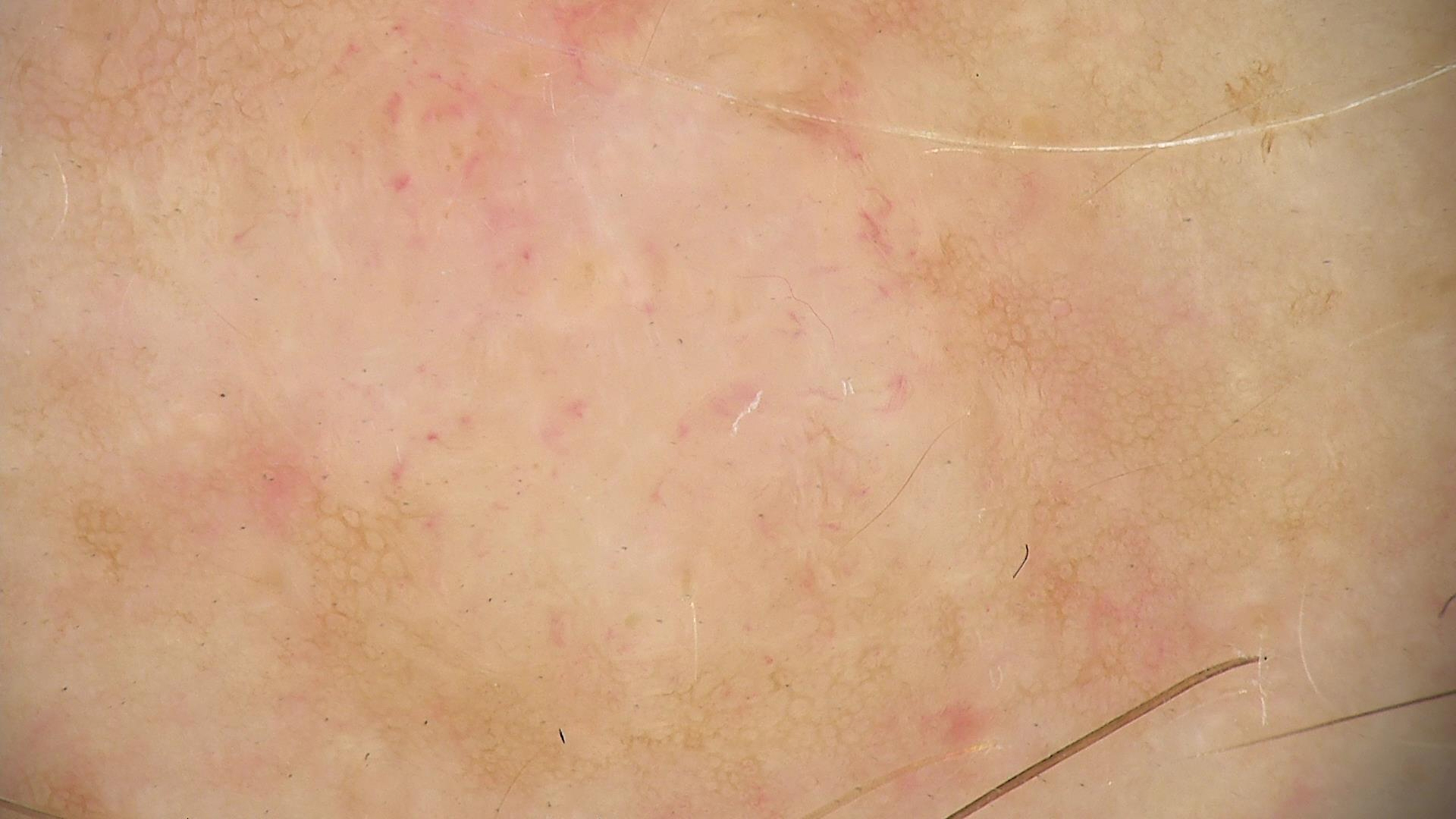{"lesion_type": {"main_class": "banal", "pattern": "dermal"}, "diagnosis": {"name": "dermal nevus", "code": "db", "malignancy": "benign", "super_class": "melanocytic", "confirmation": "expert consensus"}}